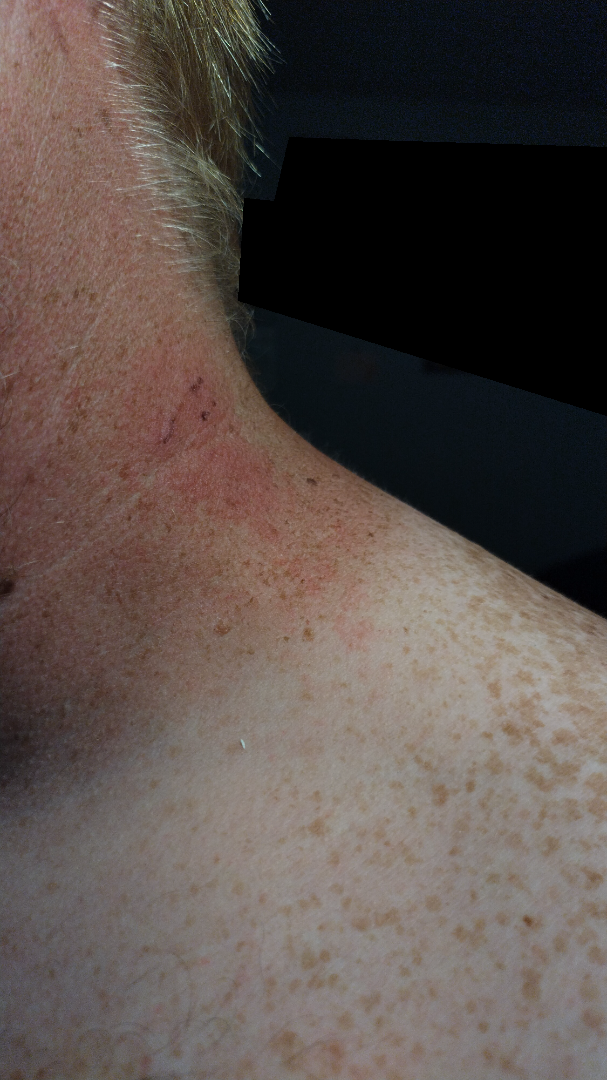On dermatologist assessment of the image: the leading impression is Allergic Contact Dermatitis.